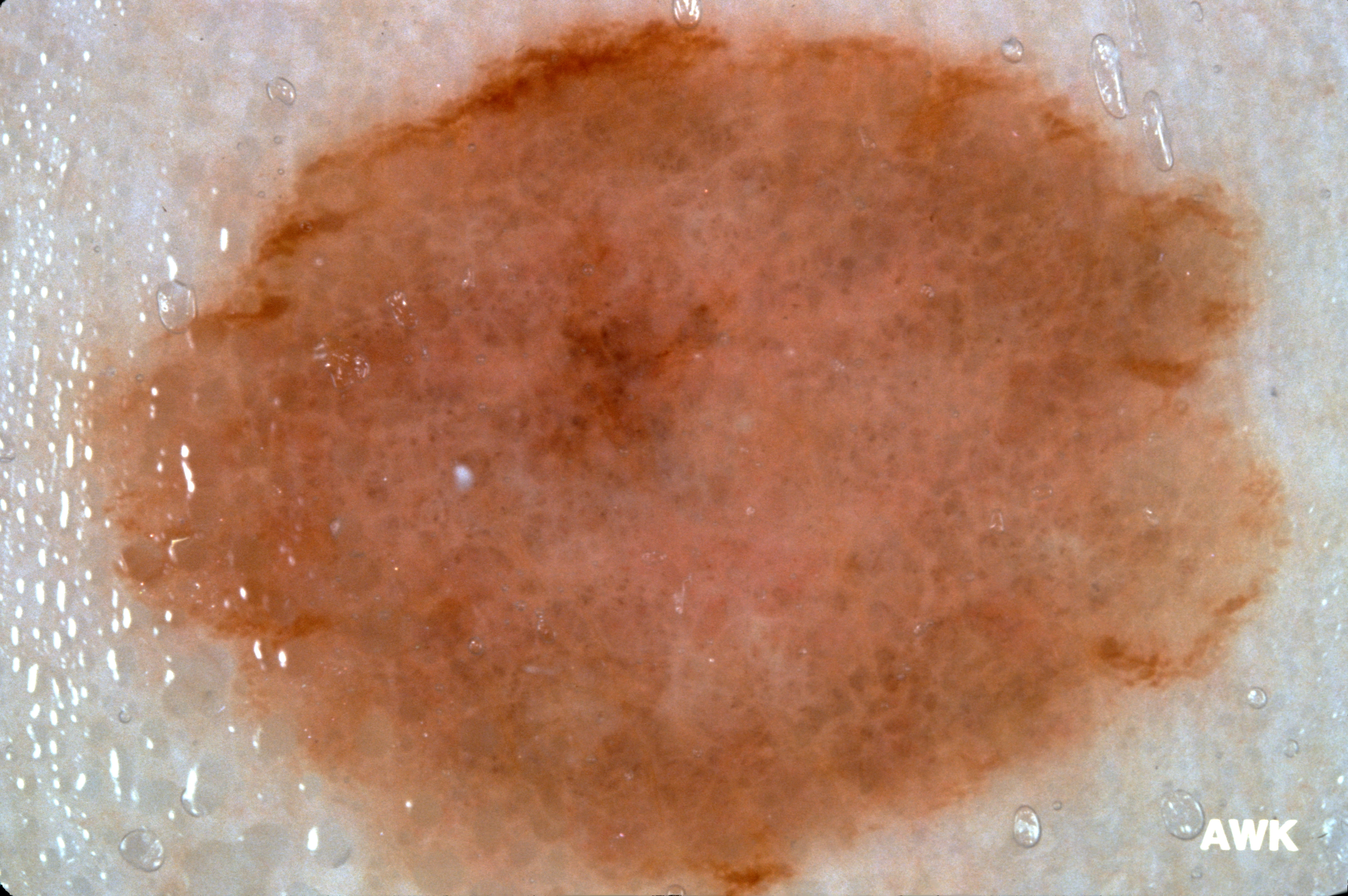A female subject, in their mid-40s. A dermoscopic view of a skin lesion. A prominent lesion filling much of the field. In (x1, y1, x2, y2) order, the lesion spans 79, 6, 1290, 895. Part of the lesion extends beyond the imaged area. Dermoscopically, the lesion shows negative network; no milia-like cysts, pigment network, or streaks. Consistent with a melanocytic nevus, a benign skin lesion.